A male subject 61 years of age · a clinical close-up photograph of a skin lesion.
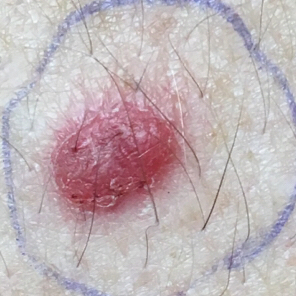region: the abdomen | reported symptoms: growth, change in appearance, itching, pain, bleeding, elevation | diagnosis: squamous cell carcinoma (biopsy-proven).